The leg is involved. An image taken at a distance. The patient is a female aged 40–49 — 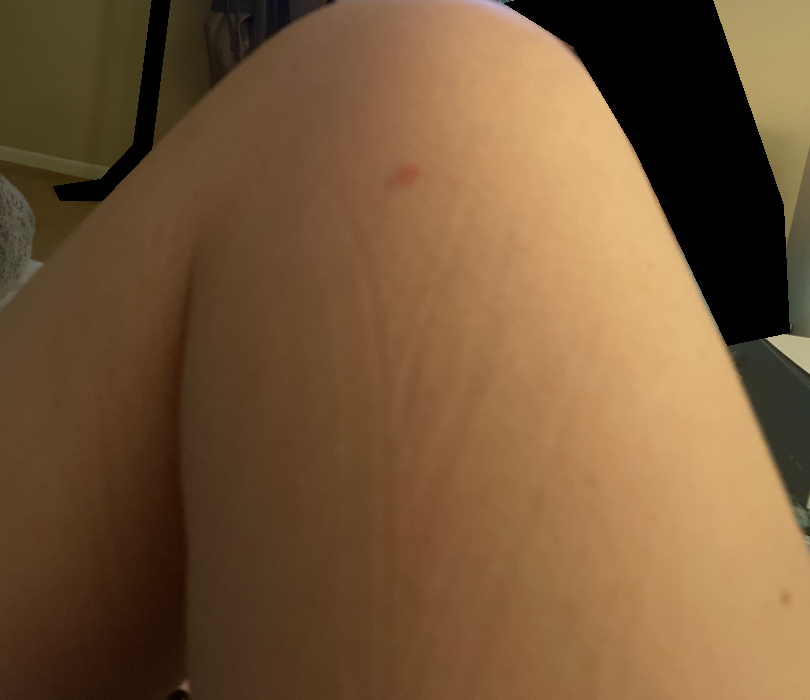No differential diagnosis could be assigned on photographic review. Reported duration is less than one week. Texture is reported as raised or bumpy. The contributor reports itching.